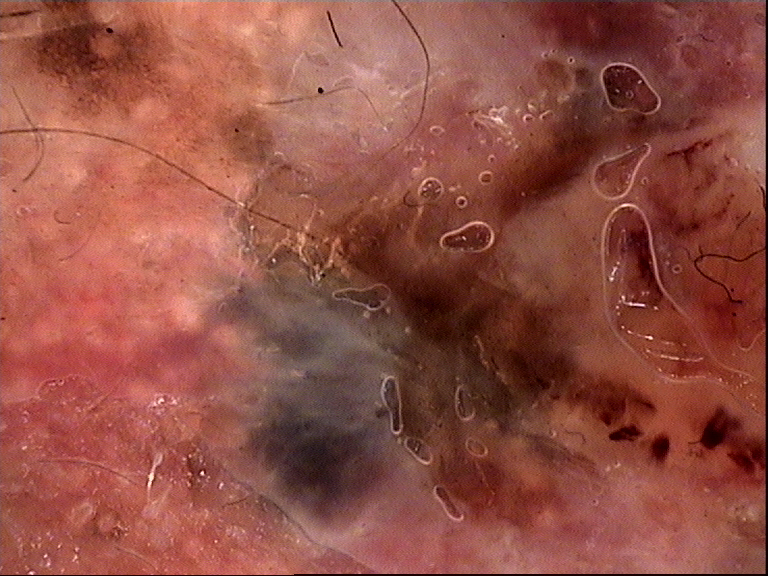A dermatoscopic image of a skin lesion. This is a keratinocytic lesion. Histopathologically confirmed as a malignancy — a basal cell carcinoma.